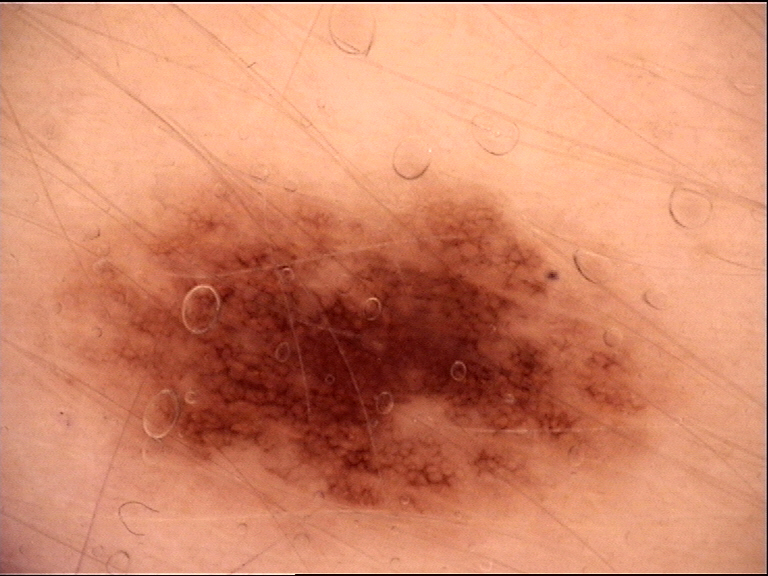A dermatoscopic image of a skin lesion. The diagnostic label was a dysplastic junctional nevus.